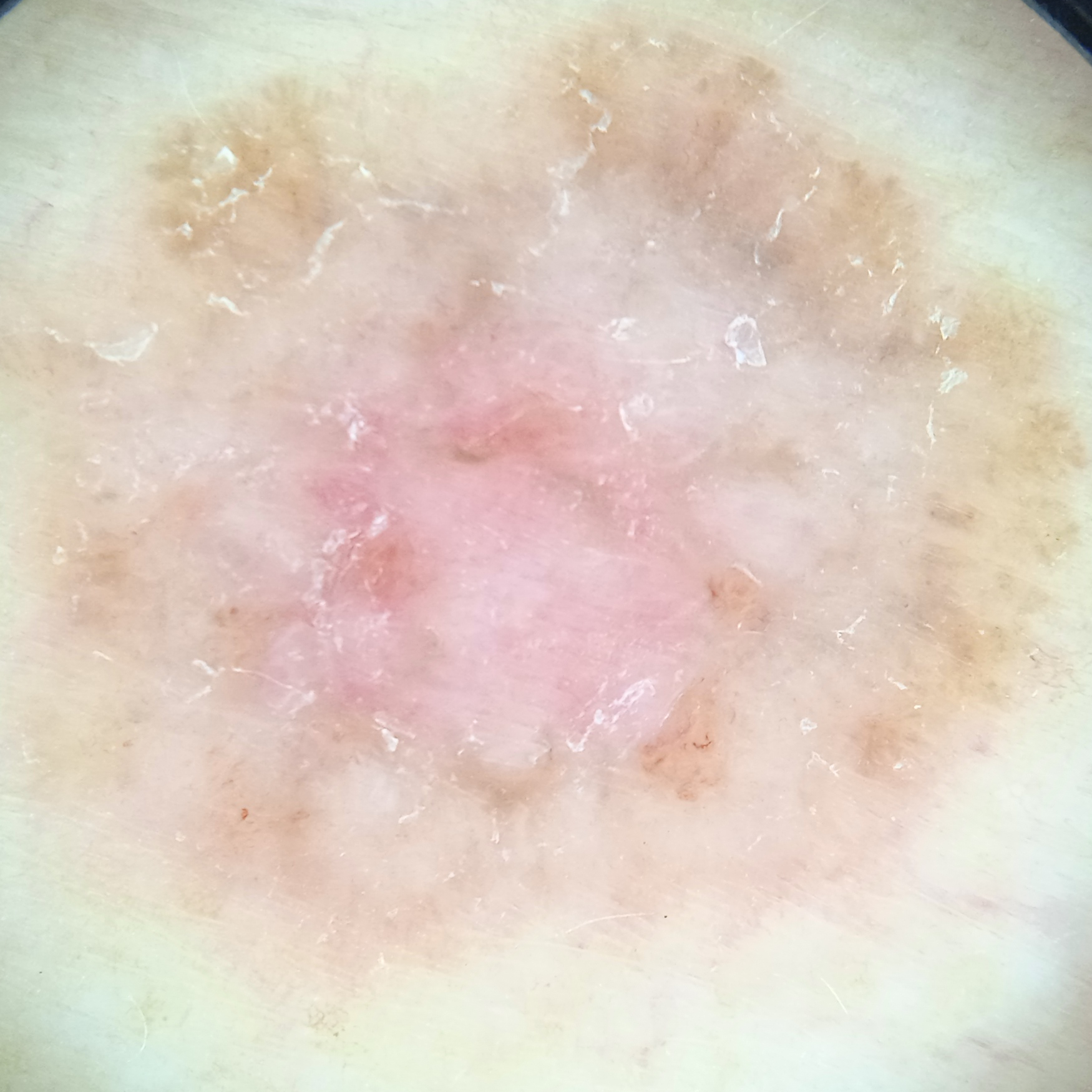| field | value |
|---|---|
| assessment | basal cell carcinoma (dermatologist consensus) |